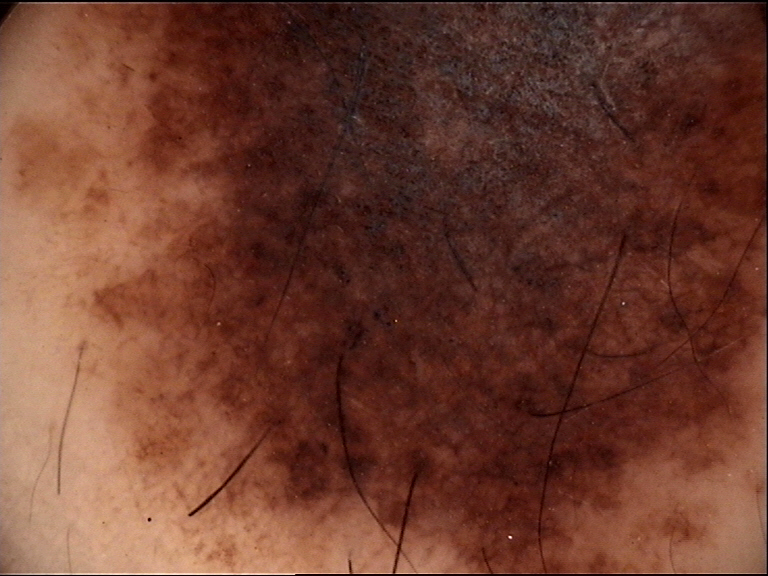Conclusion: Diagnosed as a congenital compound nevus.